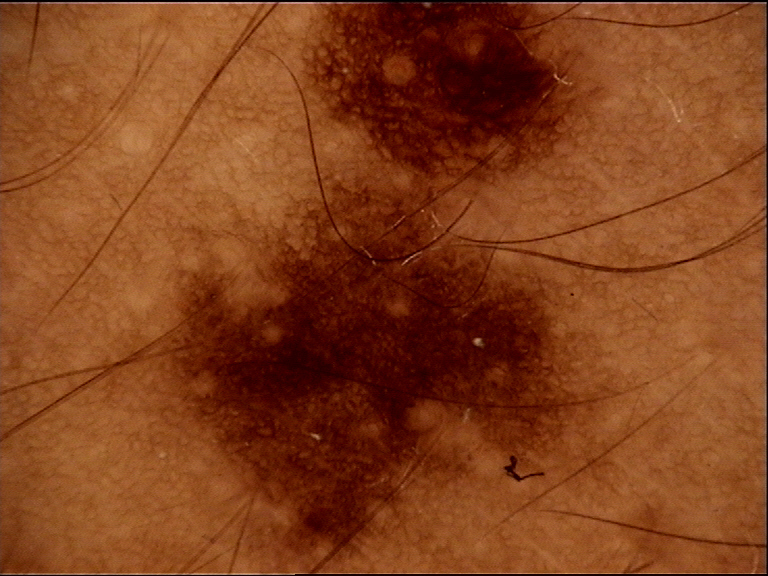Impression: The diagnosis was a dysplastic junctional nevus.